The front of the torso, back of the torso, arm, head or neck and back of the hand are involved · an image taken at a distance · the contributor is a female aged 50–59: 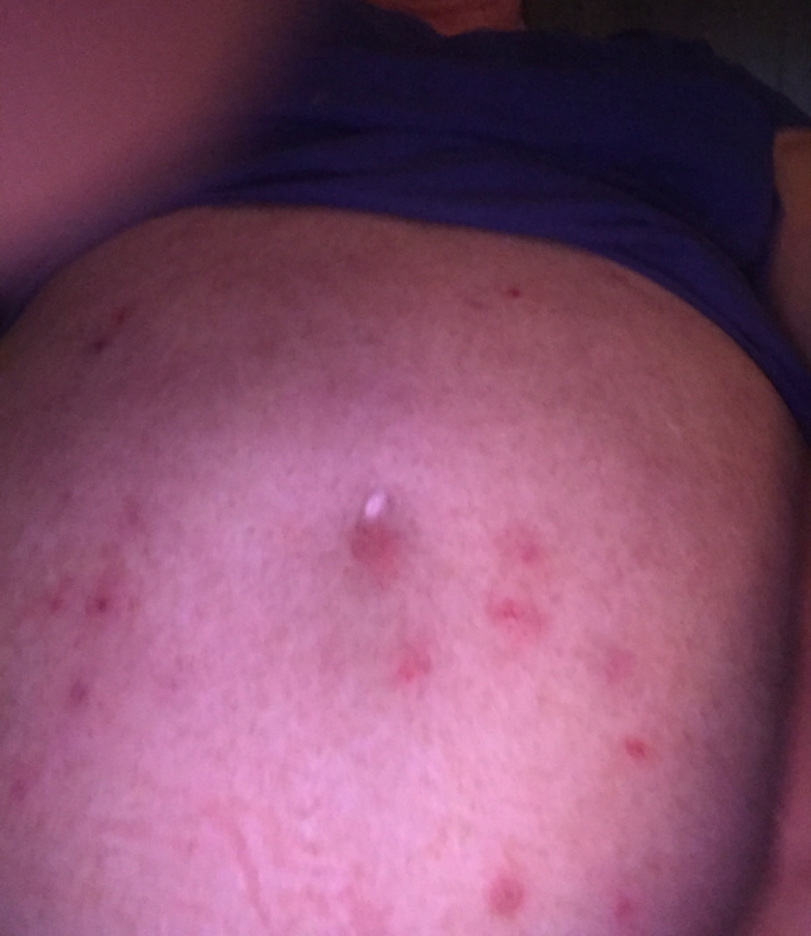patient's own categorization: a rash
symptom duration: one to four weeks
described texture: raised or bumpy
impression: the differential, in no particular order, includes Folliculitis and Insect Bite